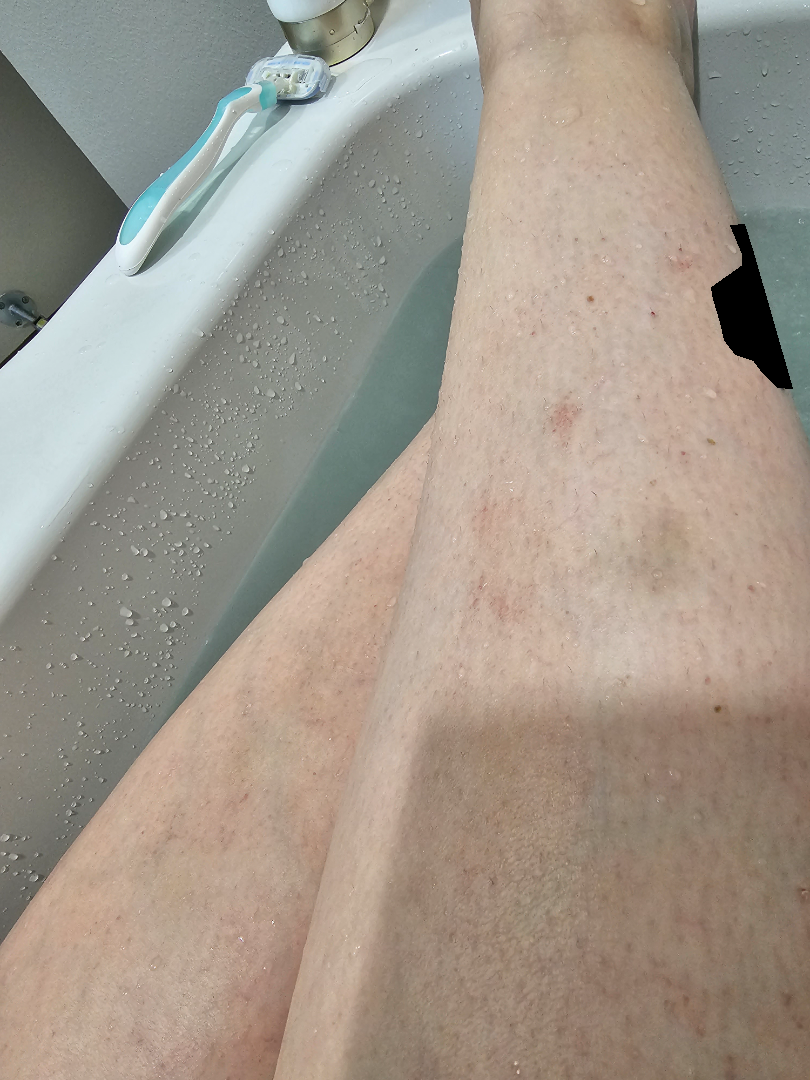Diagnostic features were not clearly distinguishable in this photograph. This image was taken at a distance. The affected area is the leg and arm.